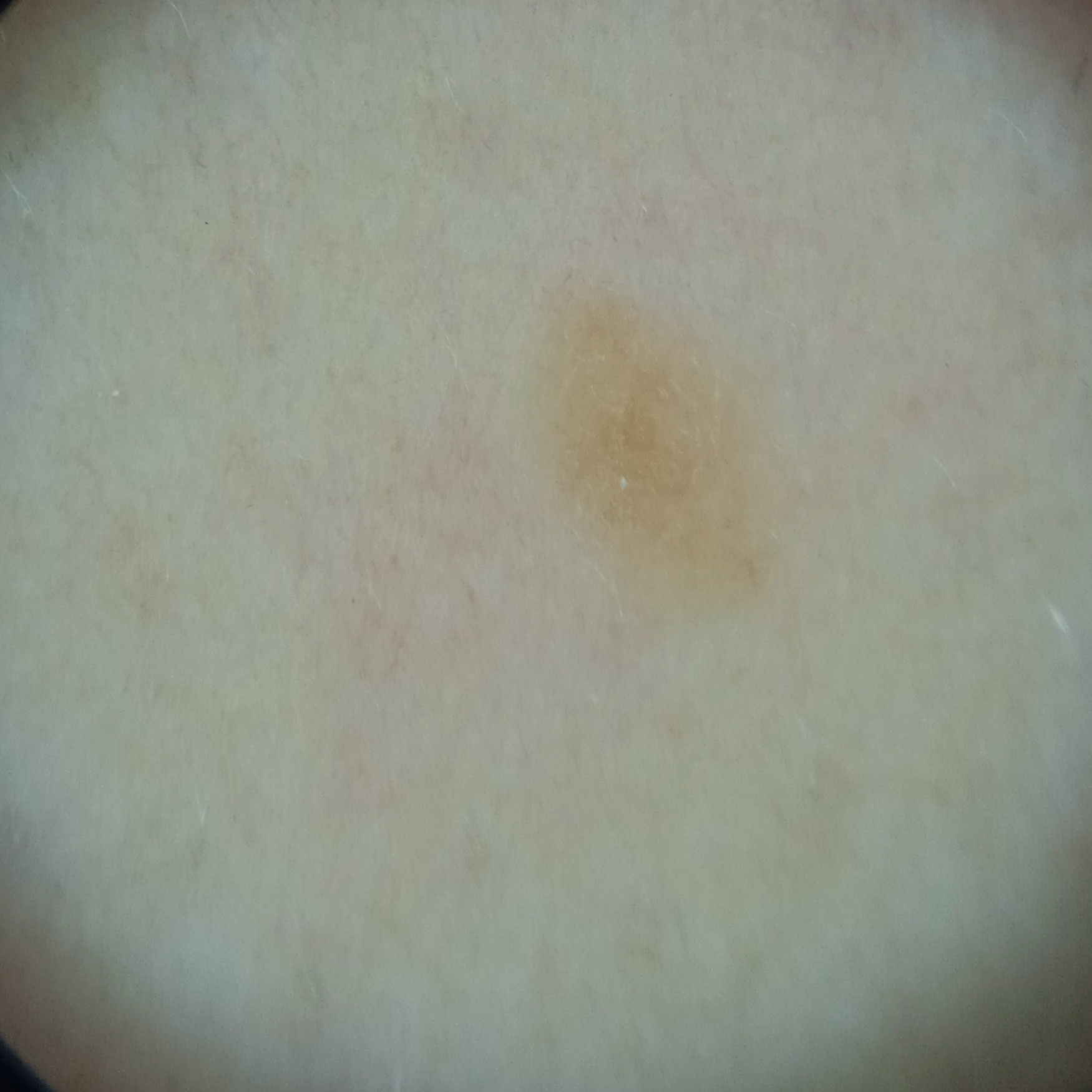A female subject 48 years old.
A dermatoscopic image of a skin lesion.
Collected as part of a research study, without a referral diagnosis.
The lesion is located on the back.
The lesion measures approximately 3.8 mm.
The dermatologists' assessment was a seborrheic keratosis.